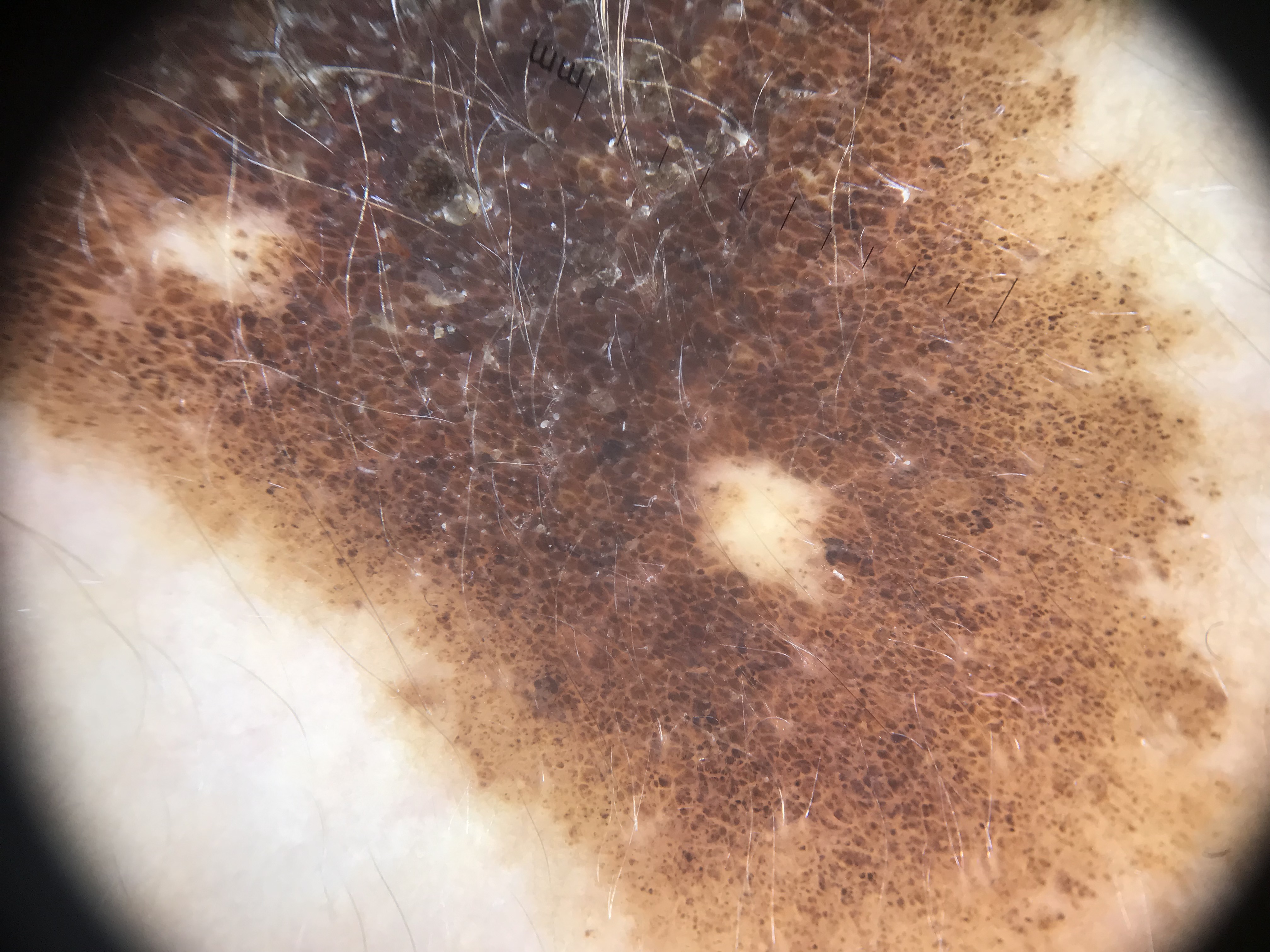The diagnosis was a congenital compound nevus.